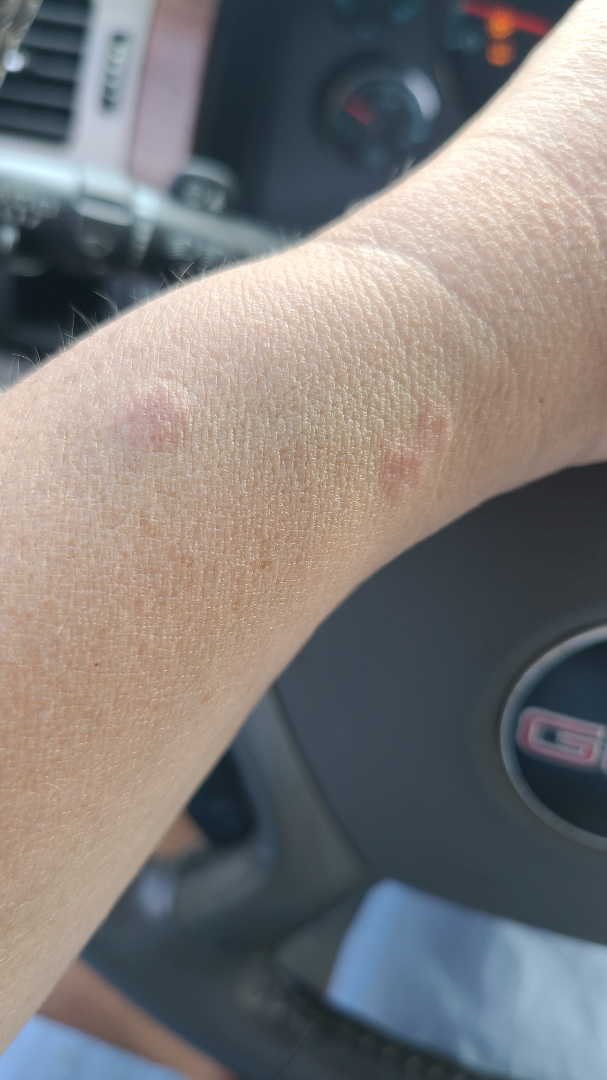| feature | finding |
|---|---|
| assessment | ungradable on photographic review |
| view | at a distance |
| affected area | arm, top or side of the foot, leg and head or neck |